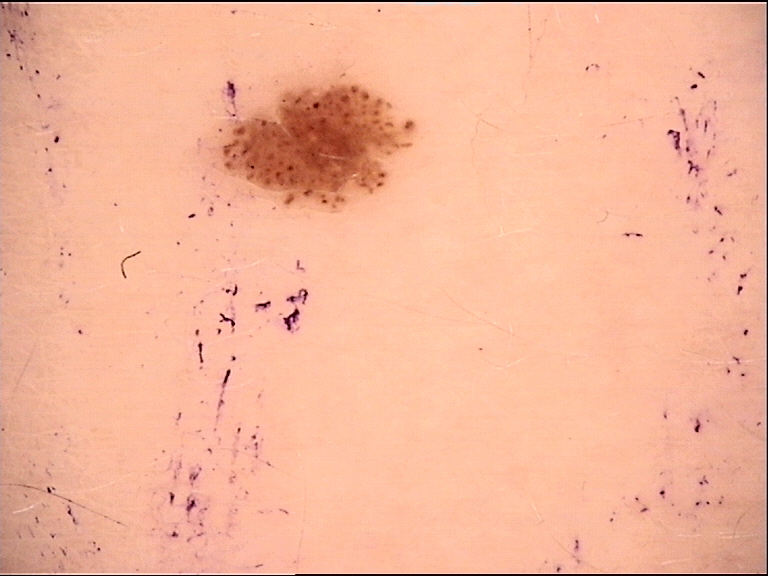Classified as a dysplastic junctional nevus.